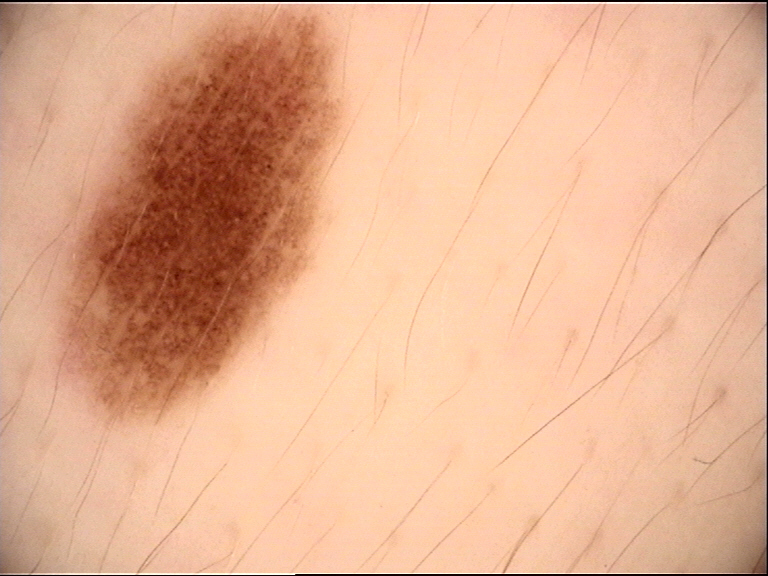The diagnostic label was a dysplastic junctional nevus.